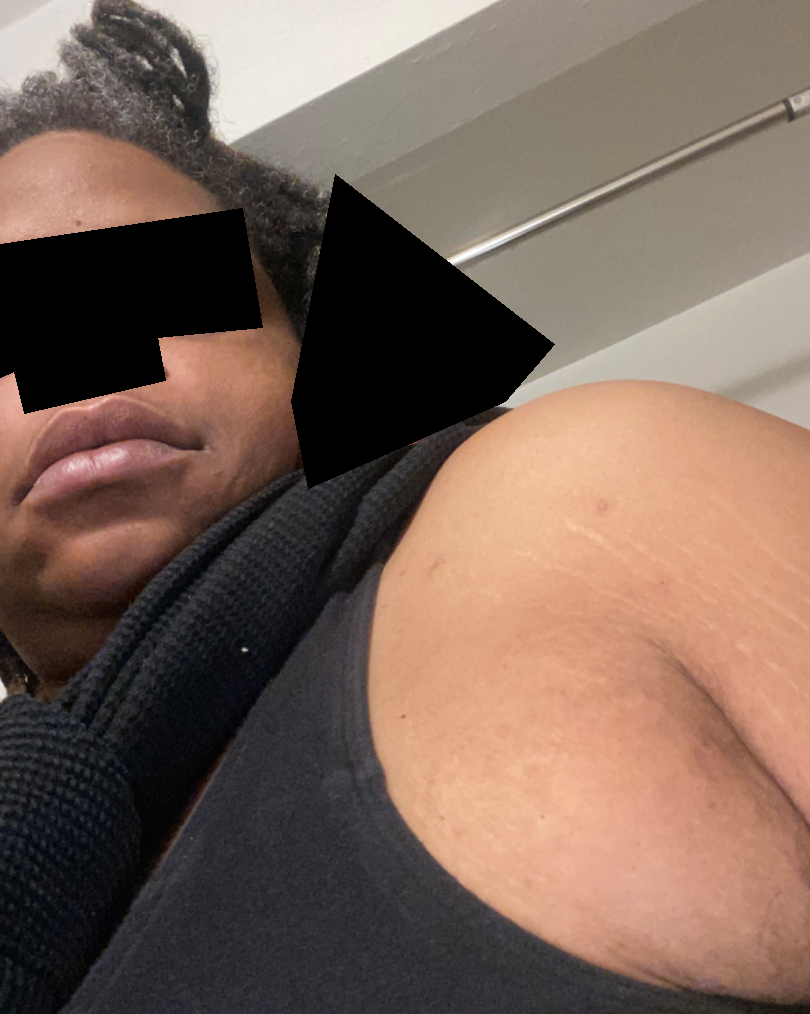The contributor is a female aged 40–49.
An image taken at a distance.
The head or neck, leg and arm are involved.
On photographic review by a dermatologist: Acne (0.50); Folliculitis (0.50).